A dermoscopic close-up of a skin lesion: 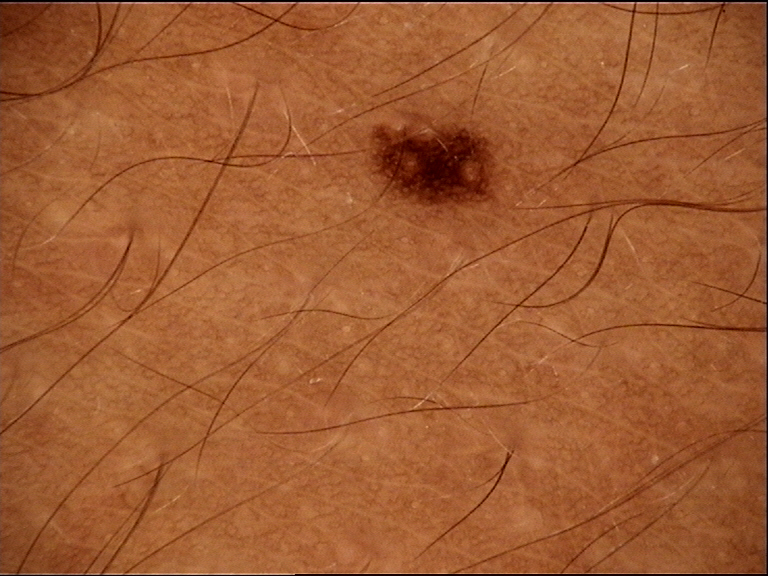Impression:
The diagnostic label was a dysplastic junctional nevus.